A dermoscopic image of a skin lesion.
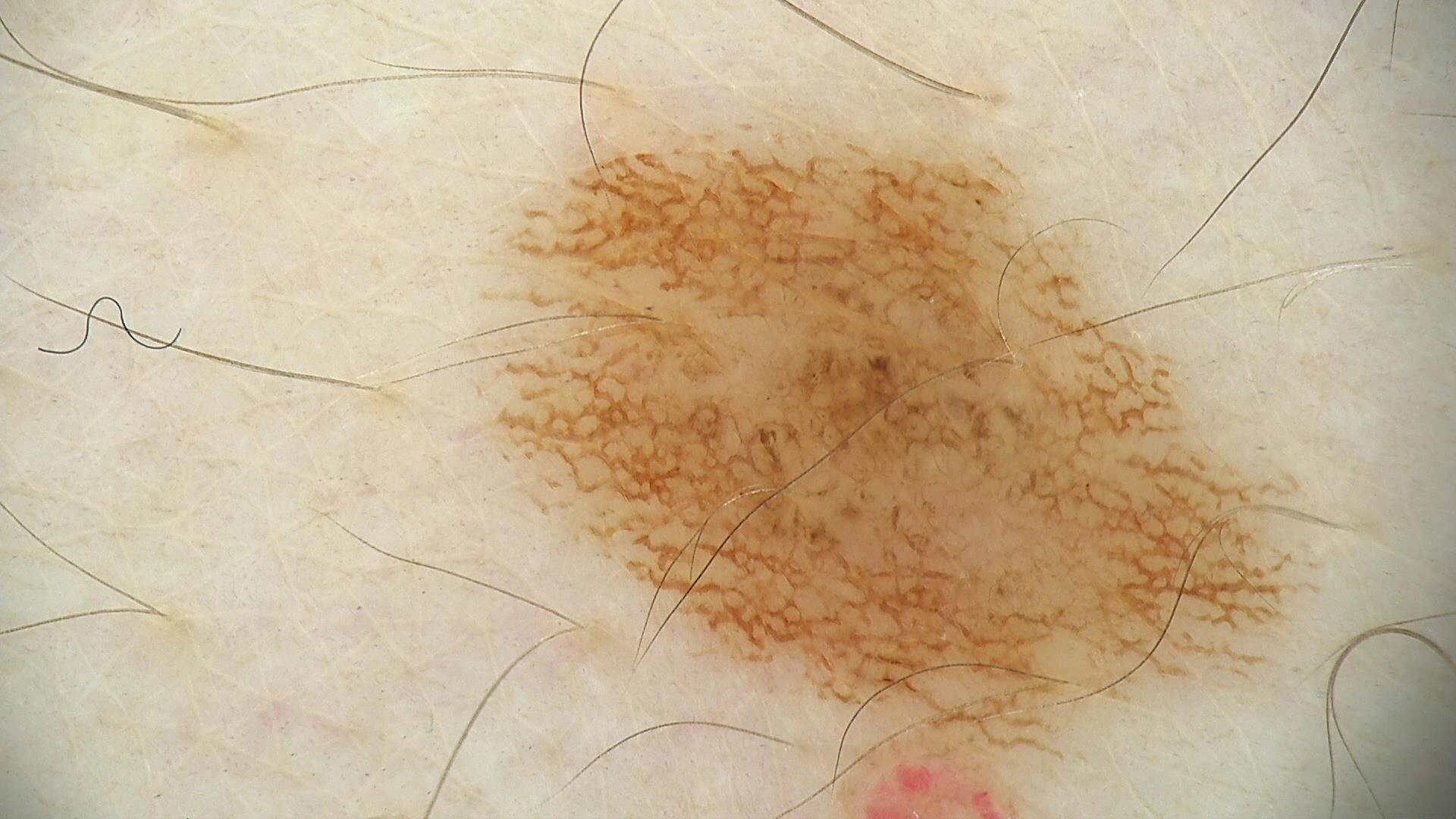– diagnostic label — dysplastic junctional nevus (expert consensus)